A female subject 78 years old. Acquired for a research image collection, with no referral diagnosis. A skin lesion imaged with a dermatoscope — 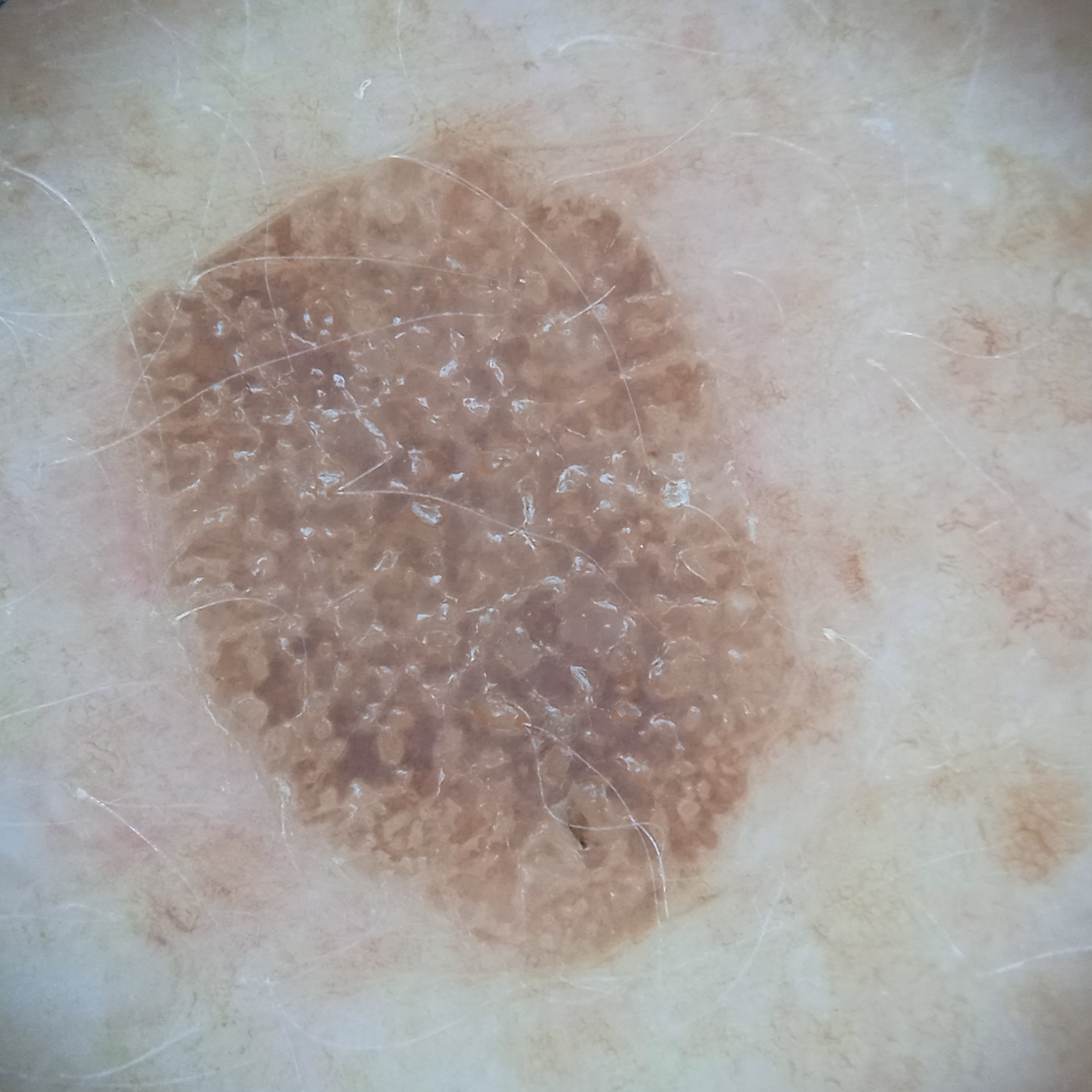Case:
- body site · the back
- assessment · seborrheic keratosis (dermatologist consensus)